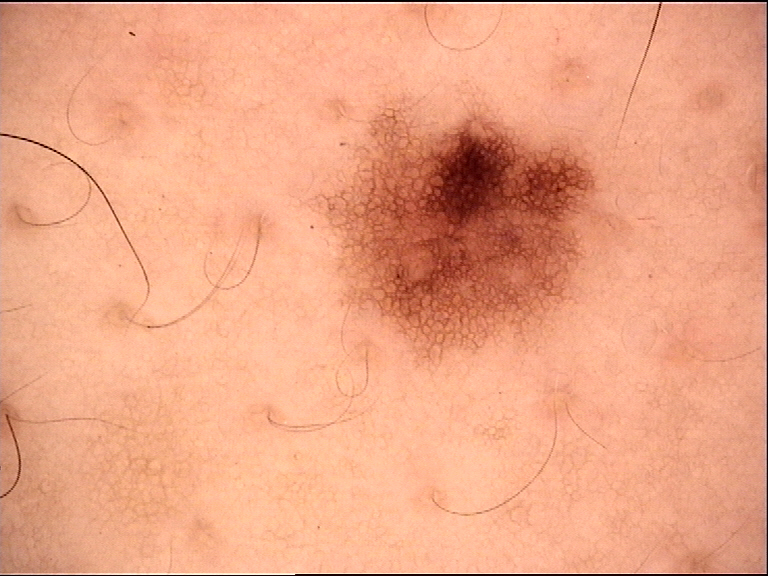Q: What kind of image is this?
A: dermoscopy
Q: What was the diagnostic impression?
A: junctional nevus (expert consensus)